A dermoscopic photograph of a skin lesion:
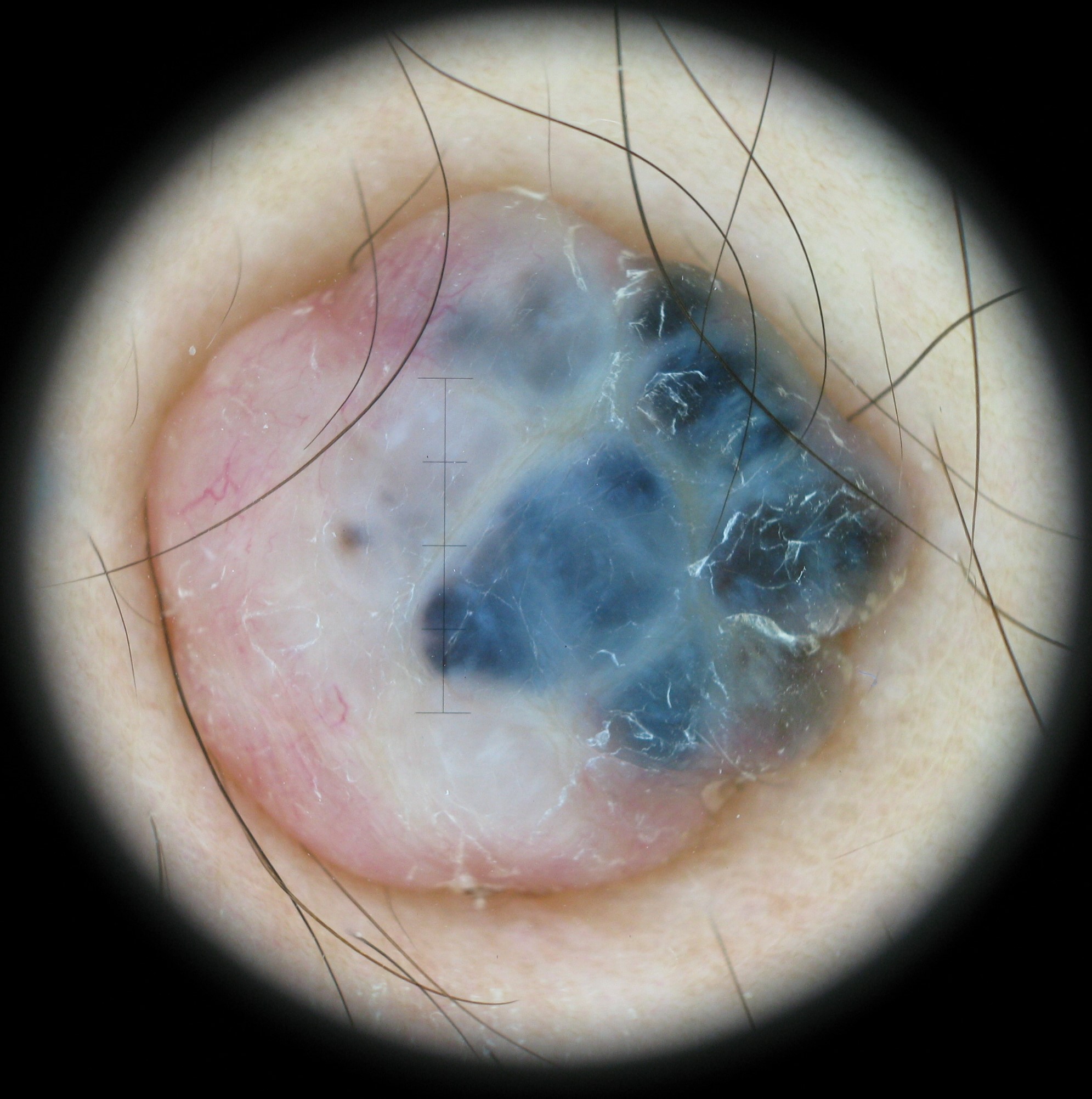class=angiokeratoma (expert consensus).